A dermatoscopic image of a skin lesion: 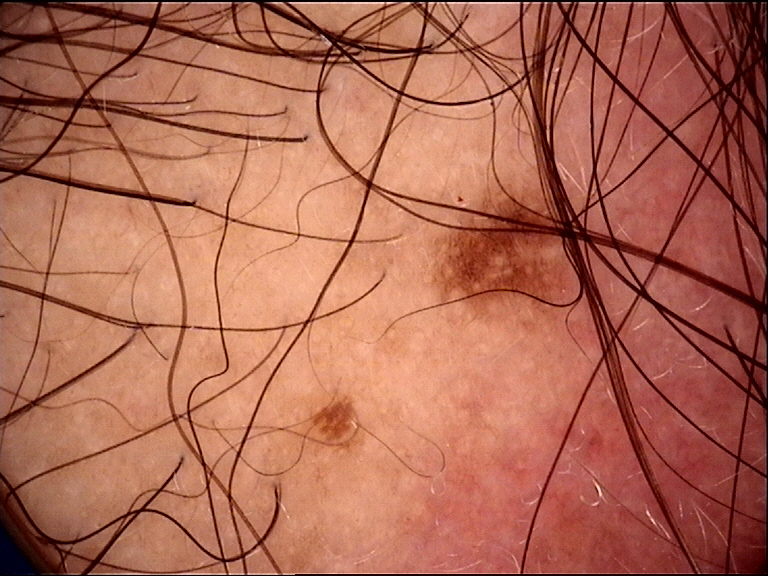The diagnostic label was a benign lesion — a dysplastic junctional nevus.